The photo was captured at a distance.
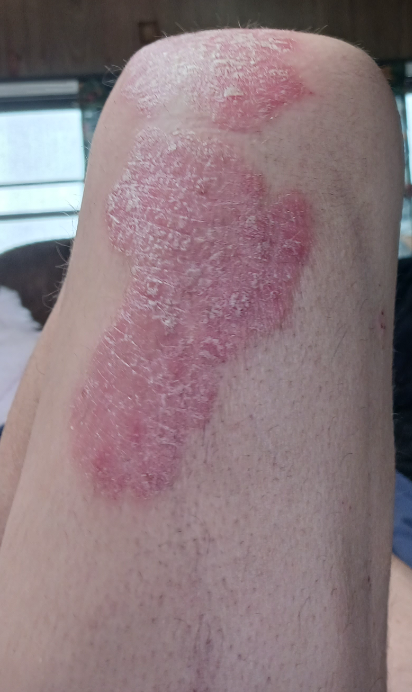– differential diagnosis — in keeping with Psoriasis